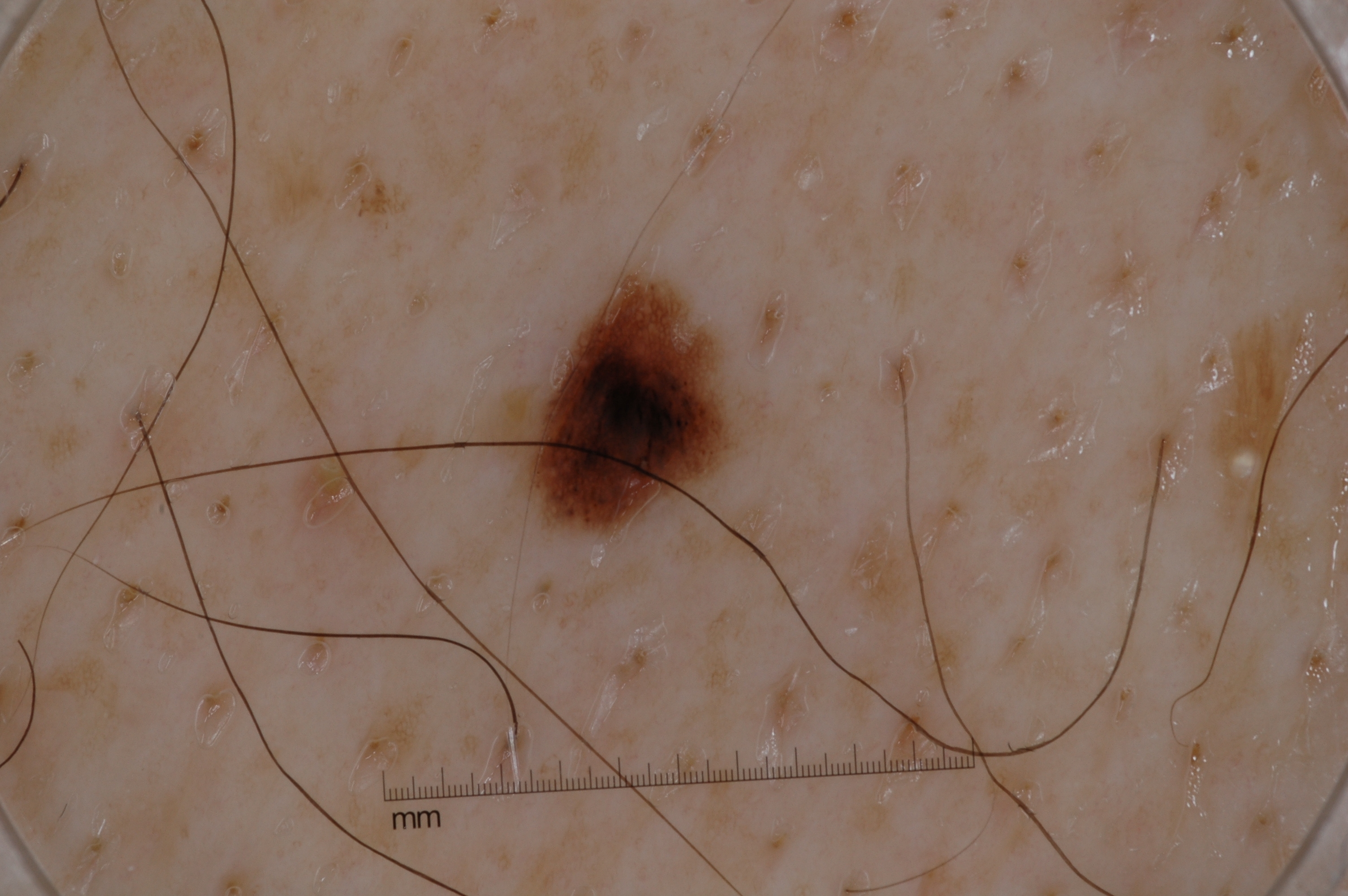Q: What is the imaging modality?
A: dermoscopy of a skin lesion
Q: Who is the patient?
A: male, in their mid-60s
Q: Which dermoscopic features were noted?
A: pigment network; absent: streaks, negative network, and milia-like cysts
Q: Where is the lesion in the image?
A: 506/280/737/525
Q: What did the assessment conclude?
A: a melanocytic nevus, a benign skin lesion